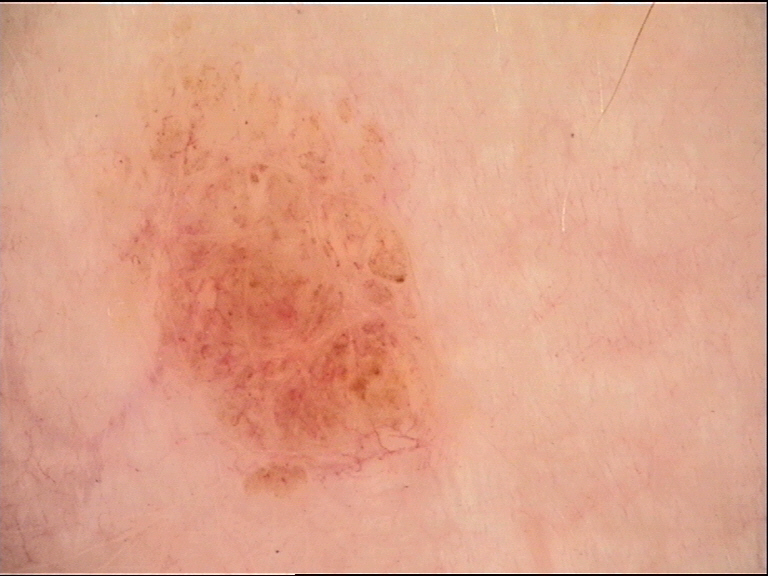diagnostic label: compound nevus (expert consensus).